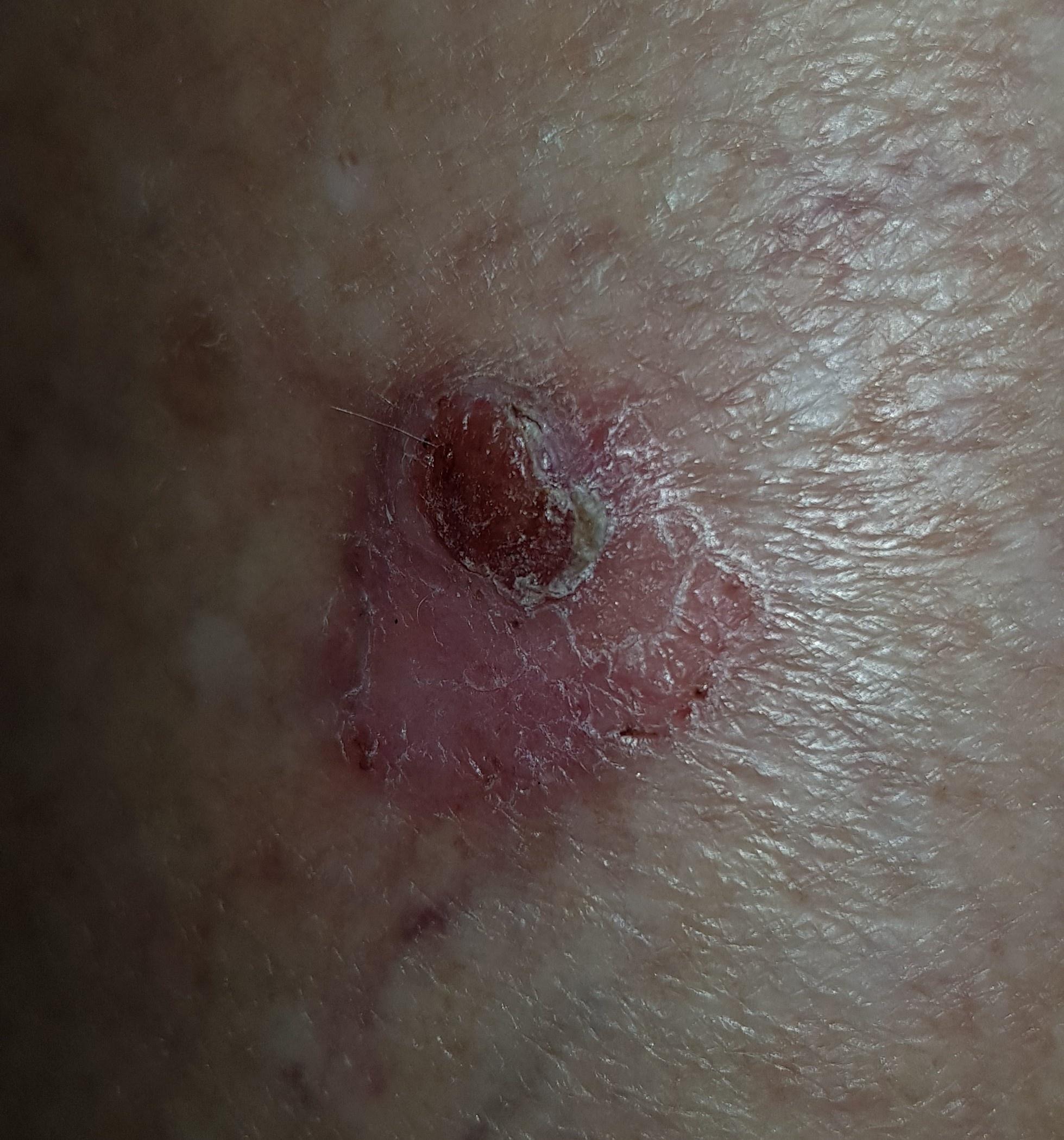<case>
  <patient>
    <age_approx>60</age_approx>
    <sex>female</sex>
  </patient>
  <skin_type>II</skin_type>
  <lesion_location>
    <region>a lower extremity</region>
  </lesion_location>
  <diagnosis>
    <name>Basal cell carcinoma</name>
    <malignancy>malignant</malignancy>
    <confirmation>histopathology</confirmation>
    <lineage>adnexal</lineage>
  </diagnosis>
</case>